A clinical photo of a skin lesion taken with a smartphone. A subject in their late 30s: 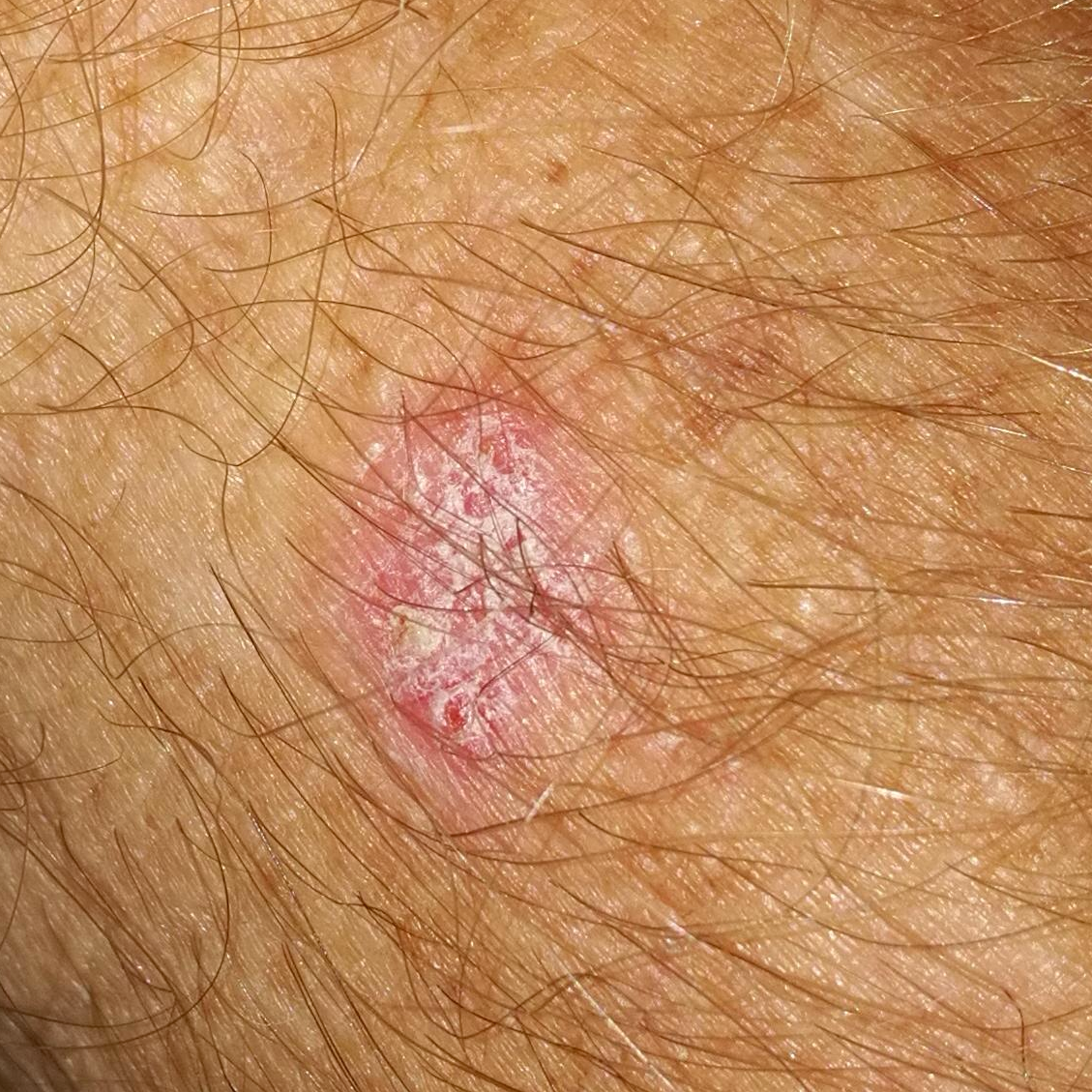Located on a forearm.
The patient reports that the lesion itches and has grown.
The diagnostic impression was an actinic keratosis.